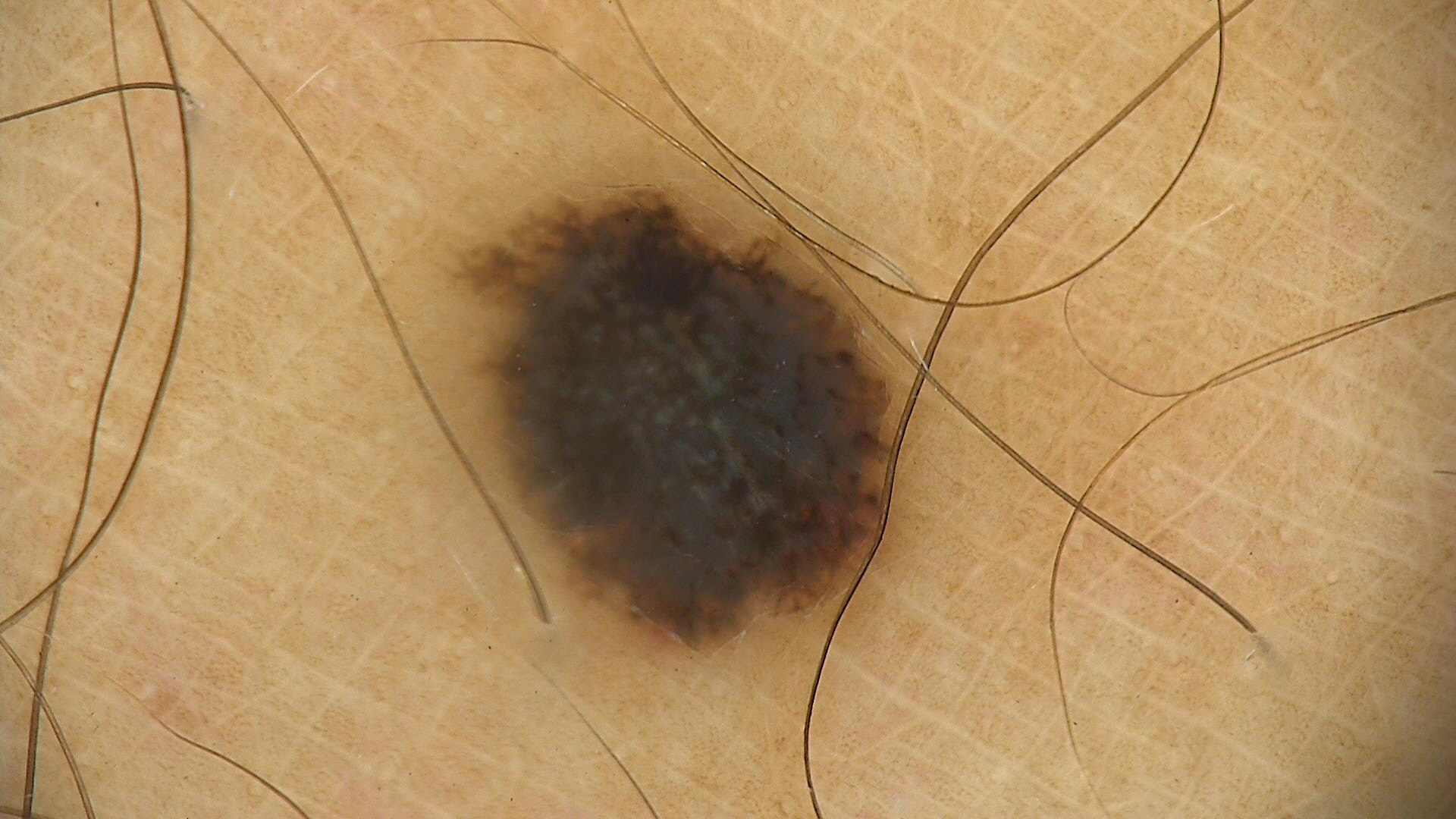| key | value |
|---|---|
| pathology | melanoma (biopsy-proven) |